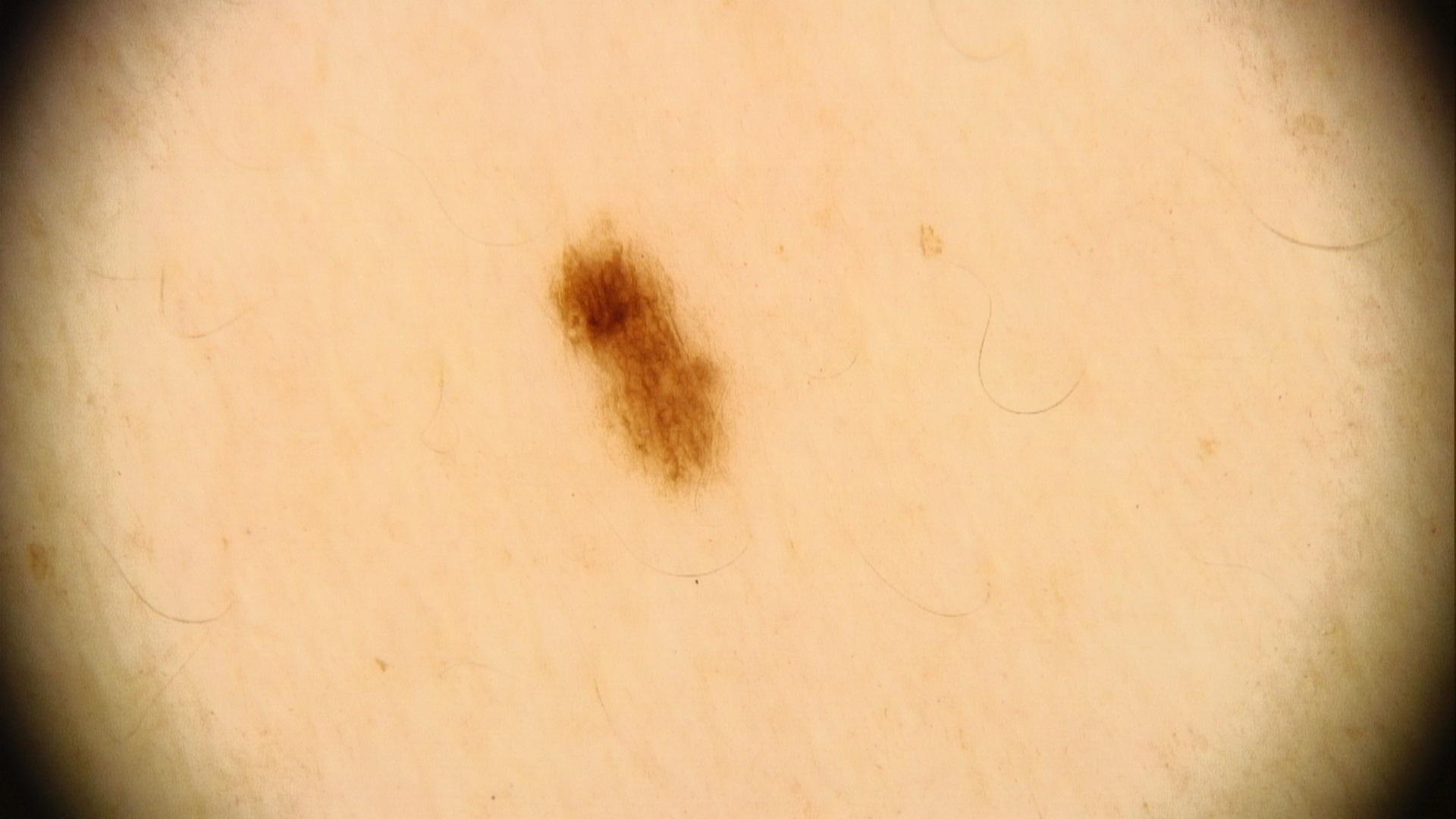Findings: A female patient in their mid-30s. The chart records melanoma in a first-degree relative but no previous melanoma. Recorded as Fitzpatrick skin type III. The lesion was found on the trunk. Conclusion: The clinical assessment was a nevus.